The photograph was taken at an angle · the patient is a female aged 30–39 · the lesion involves the top or side of the foot:
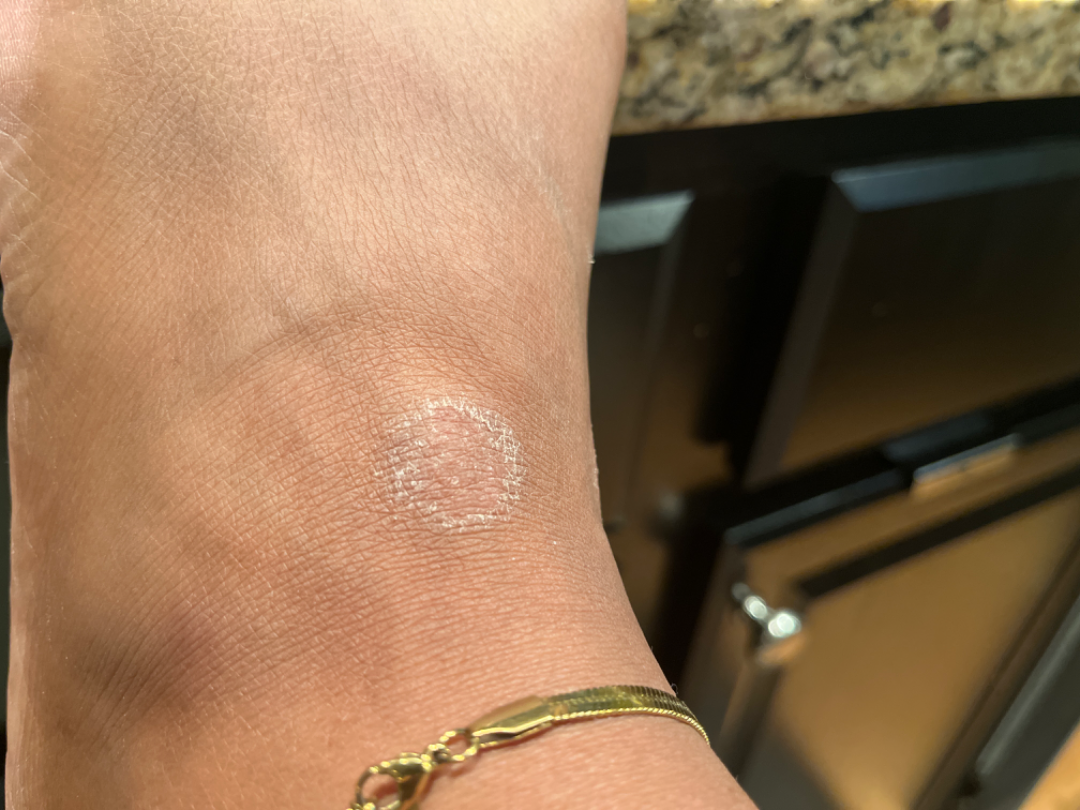On dermatologist assessment of the image: the leading consideration is Eczema; possibly Tinea.